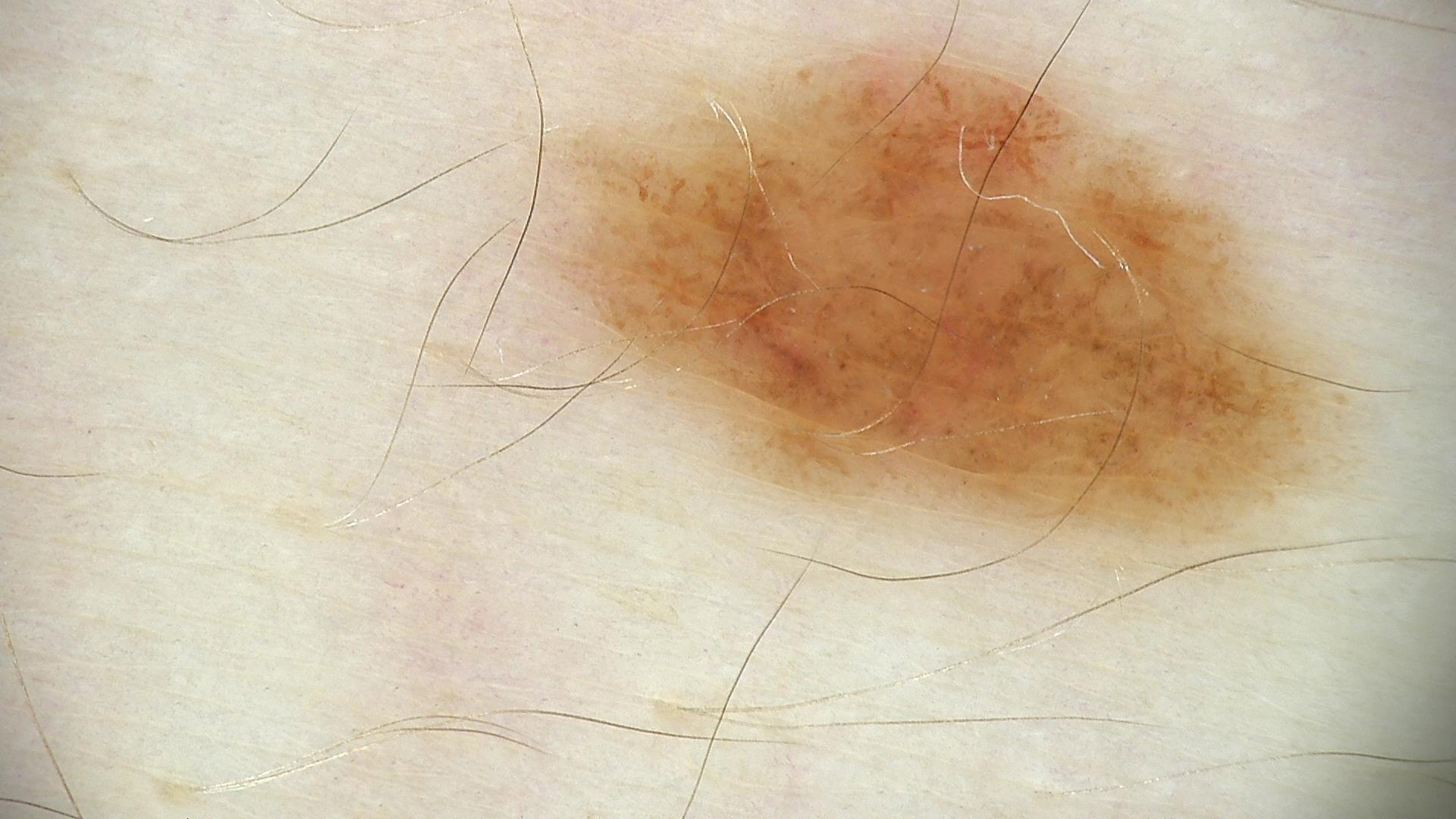diagnosis:
  name: dysplastic junctional nevus
  code: jd
  malignancy: benign
  super_class: melanocytic
  confirmation: expert consensus